A clinical photograph showing a skin lesion in context · a female subject aged around 55 · the patient is Fitzpatrick II:
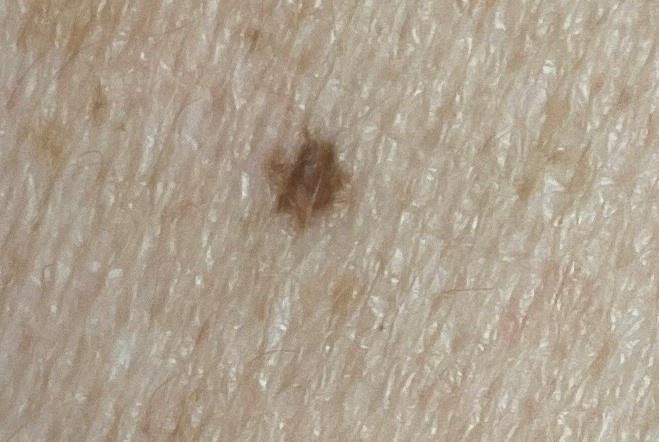The lesion is on the trunk.
The biopsy diagnosis was a lesion of epidermal origin — a squamous cell carcinoma.